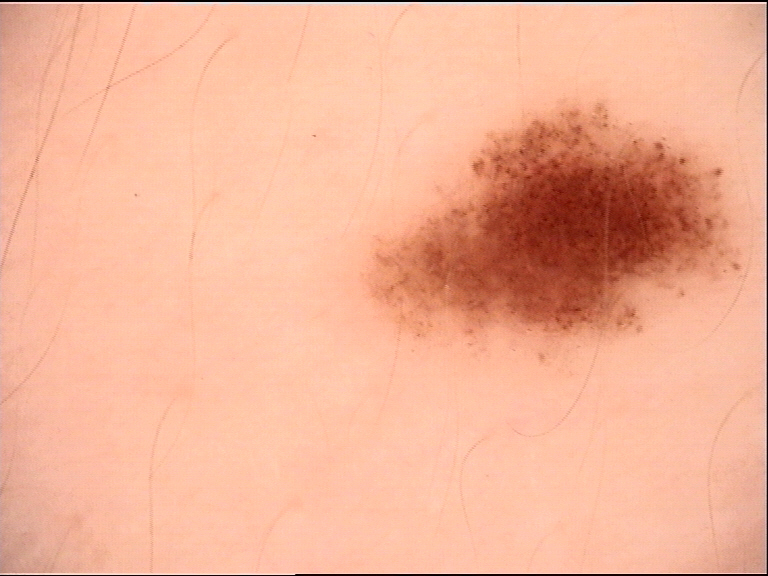Consistent with a dysplastic junctional nevus.